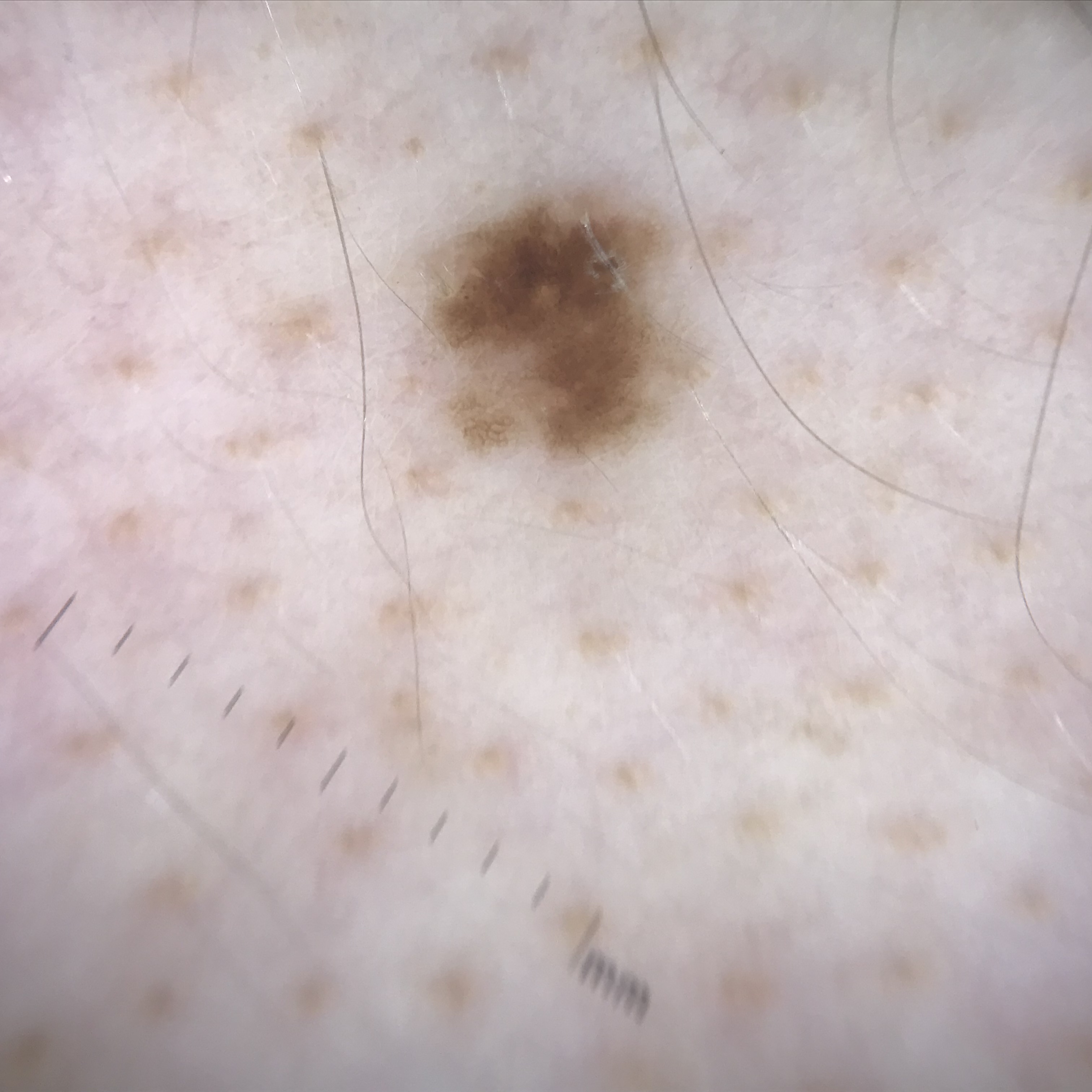Q: What was the diagnostic impression?
A: dysplastic junctional nevus (expert consensus)